This image was taken at a distance — 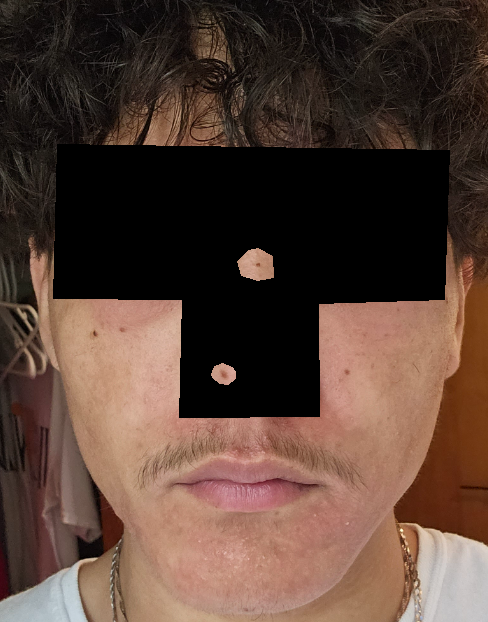The case was indeterminate on photographic review.